A dermatoscopic image of a skin lesion.
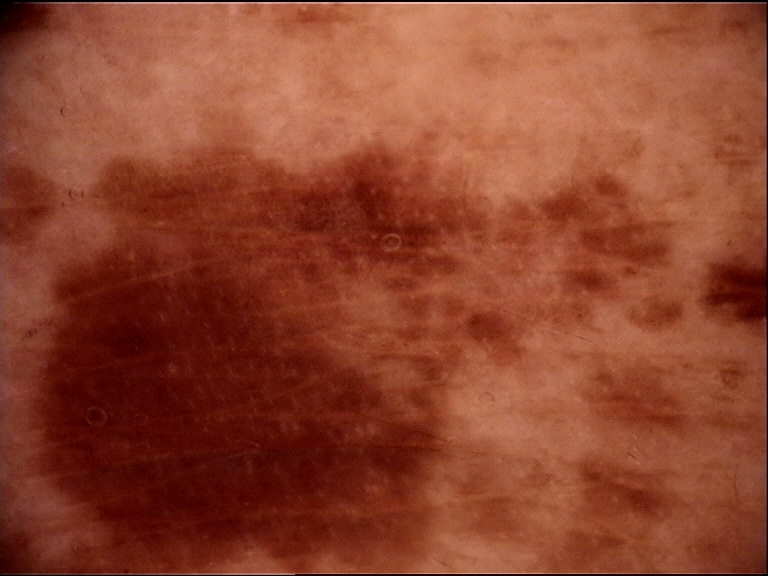Consistent with a dysplastic junctional nevus.